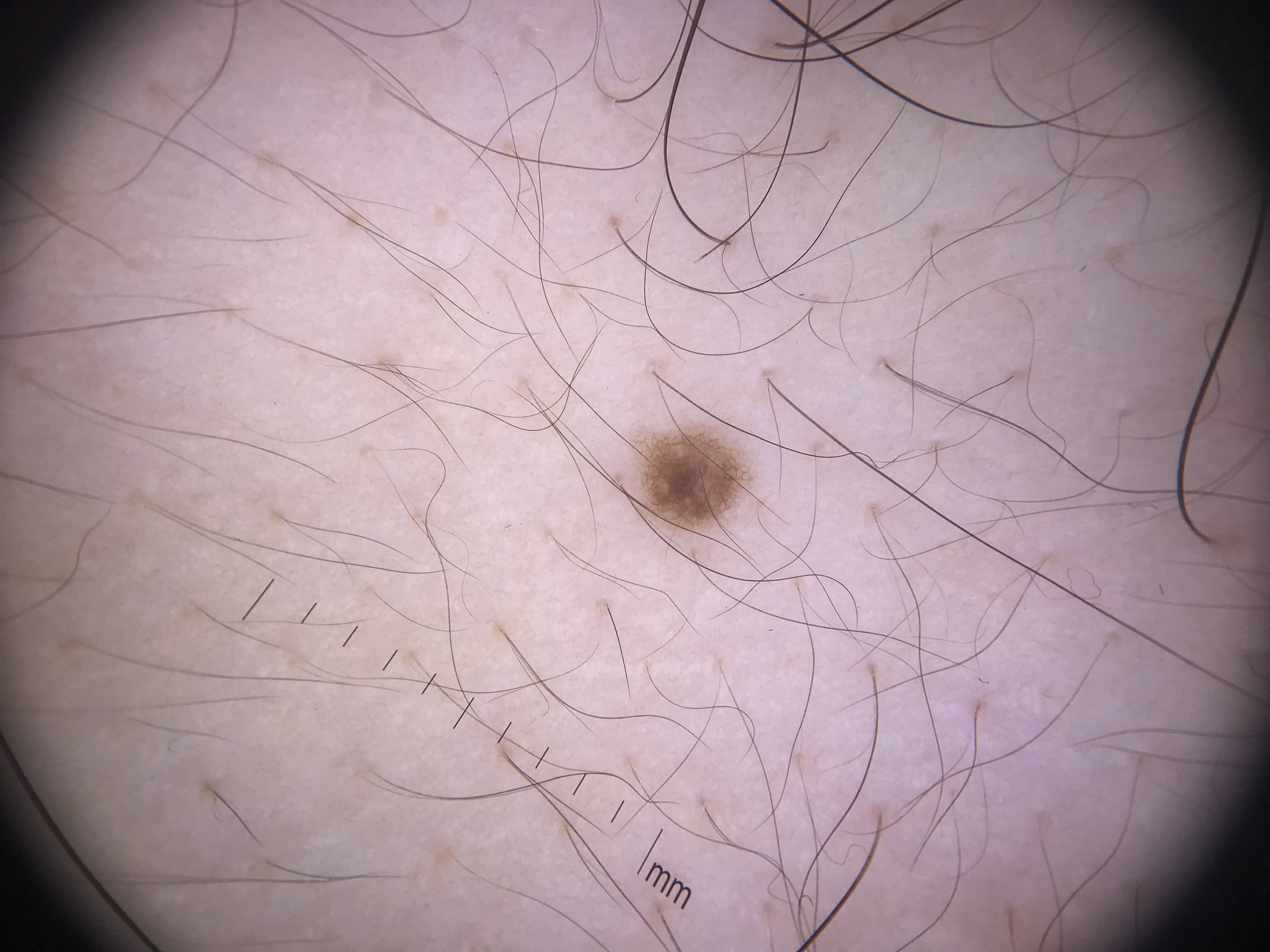Conclusion: The diagnostic label was a junctional nevus.